The lesion involves the head or neck. Female subject, age 18–29. This image was taken at a distance.
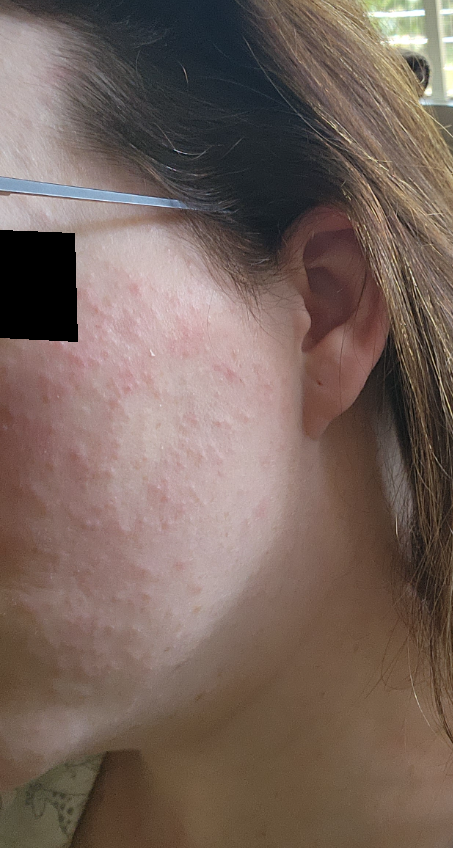On photographic review: most consistent with Rosacea; an alternative is Allergic Contact Dermatitis; a more distant consideration is Acne; less likely is Miliaria; less probable is Folliculitis.